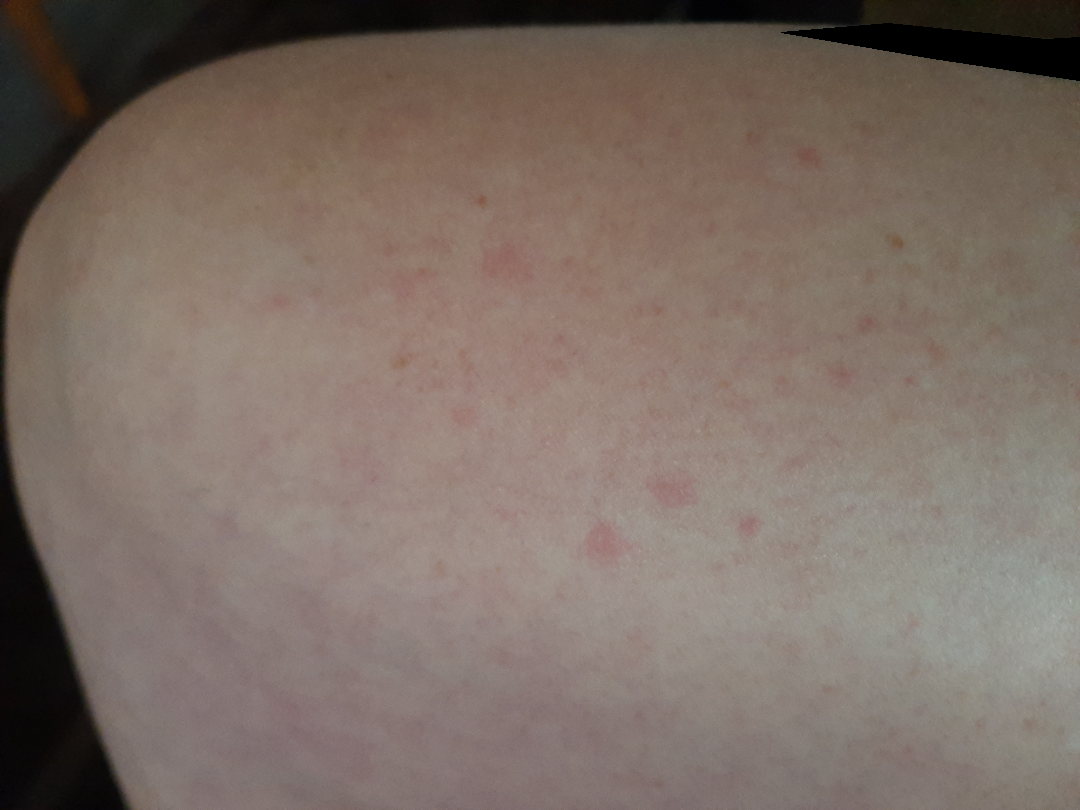assessment=could not be assessed
location=leg and arm
view=close-up
skin tone=Fitzpatrick skin type III; lay graders estimated 2 on the Monk skin tone scale
texture=flat
present for=one to three months